A dermatoscopic image of a skin lesion.
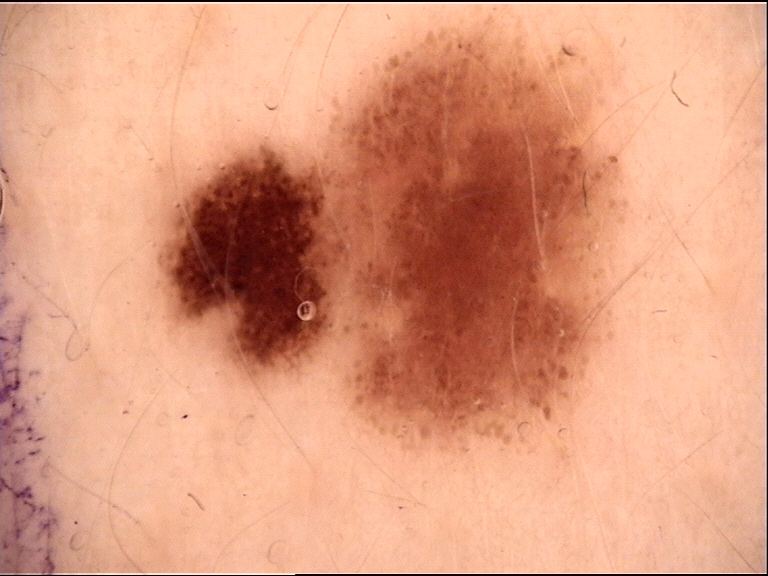Impression: Classified as a dysplastic junctional nevus.